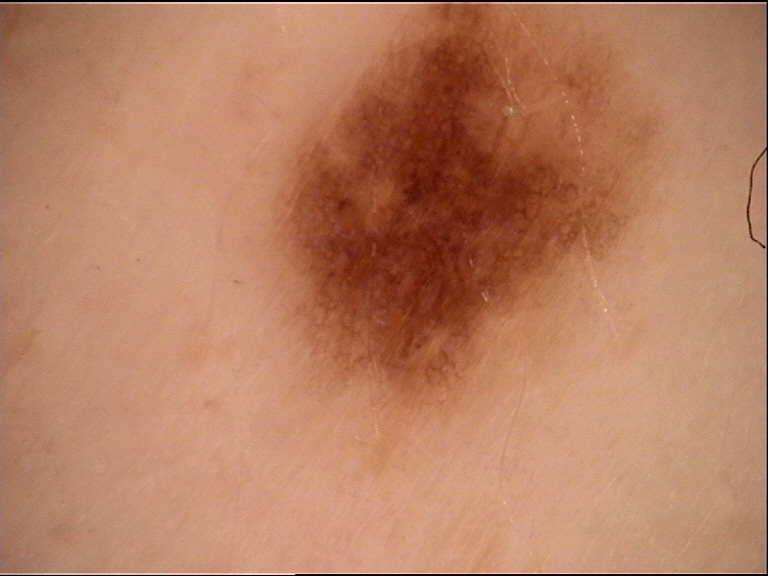Q: What is this lesion?
A: dysplastic junctional nevus (expert consensus)